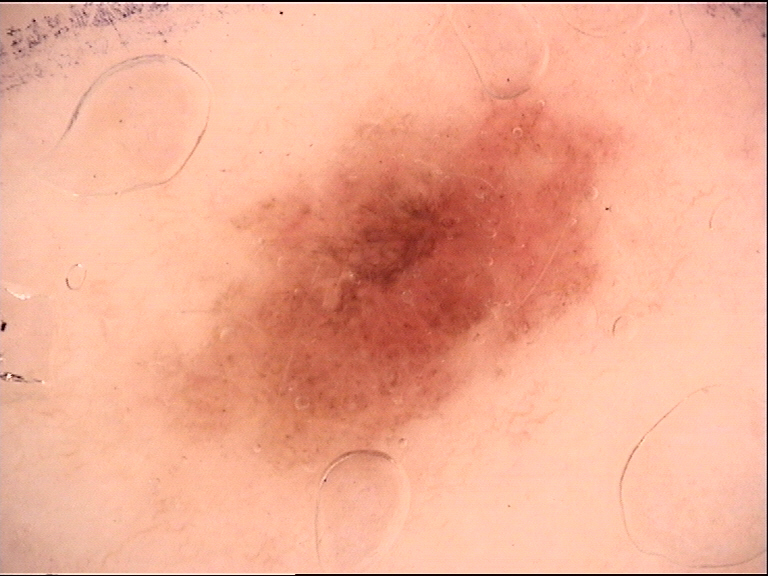Impression:
Labeled as a dysplastic junctional nevus.